This image was taken at an angle. The affected area is the top or side of the foot: 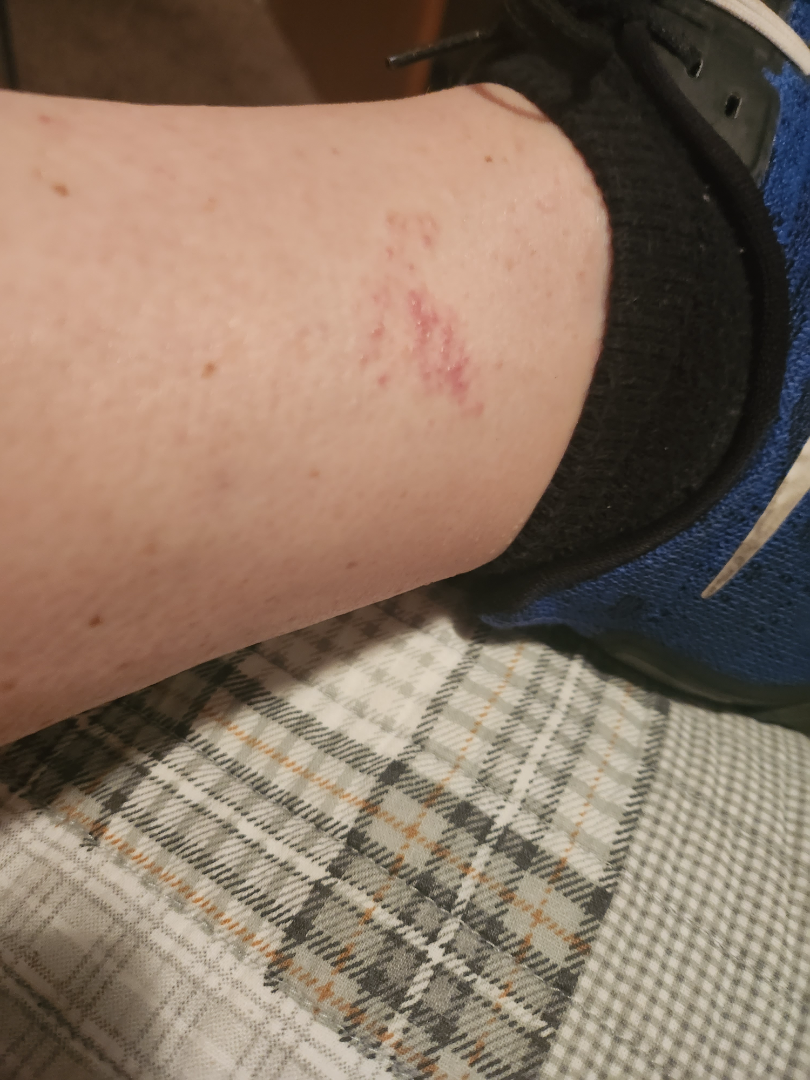Q: Could the case be diagnosed?
A: ungradable on photographic review